A close-up photograph. The patient considered this a rash. The lesion is associated with itching. The subject is a male aged 30–39. Located on the arm, back of the hand, palm and top or side of the foot. The lesion is described as fluid-filled and raised or bumpy. The condition has been present for about one day. The patient also reports fever.
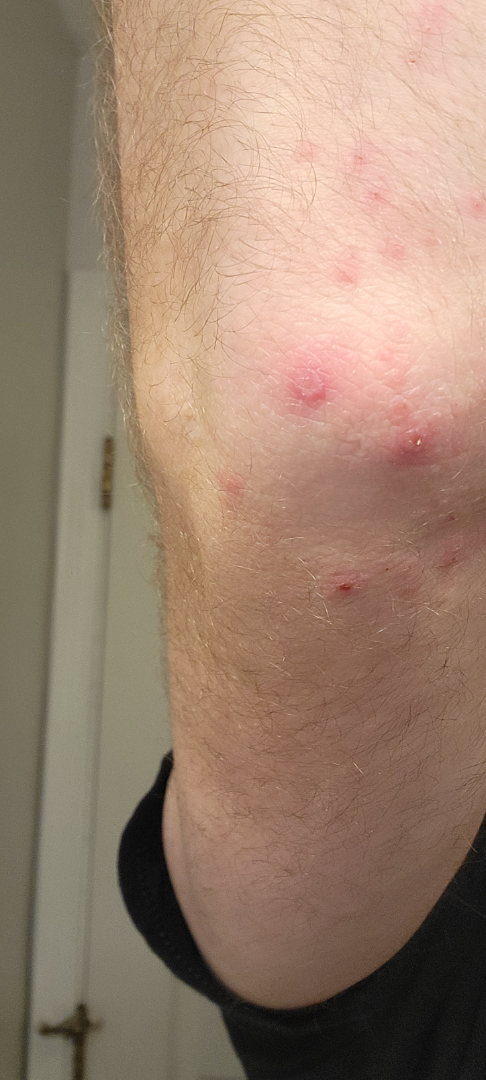<case>
<differential>
  <tied_lead>Psoriasis, Insect Bite</tied_lead>
  <unlikely>Folliculitis; Dermatitis herpetiformis; Acute dermatitis, NOS; Skin and soft tissue atypical mycobacterial infection; Perforating dermatosis</unlikely>
</differential>
</case>